This is a close-up image:
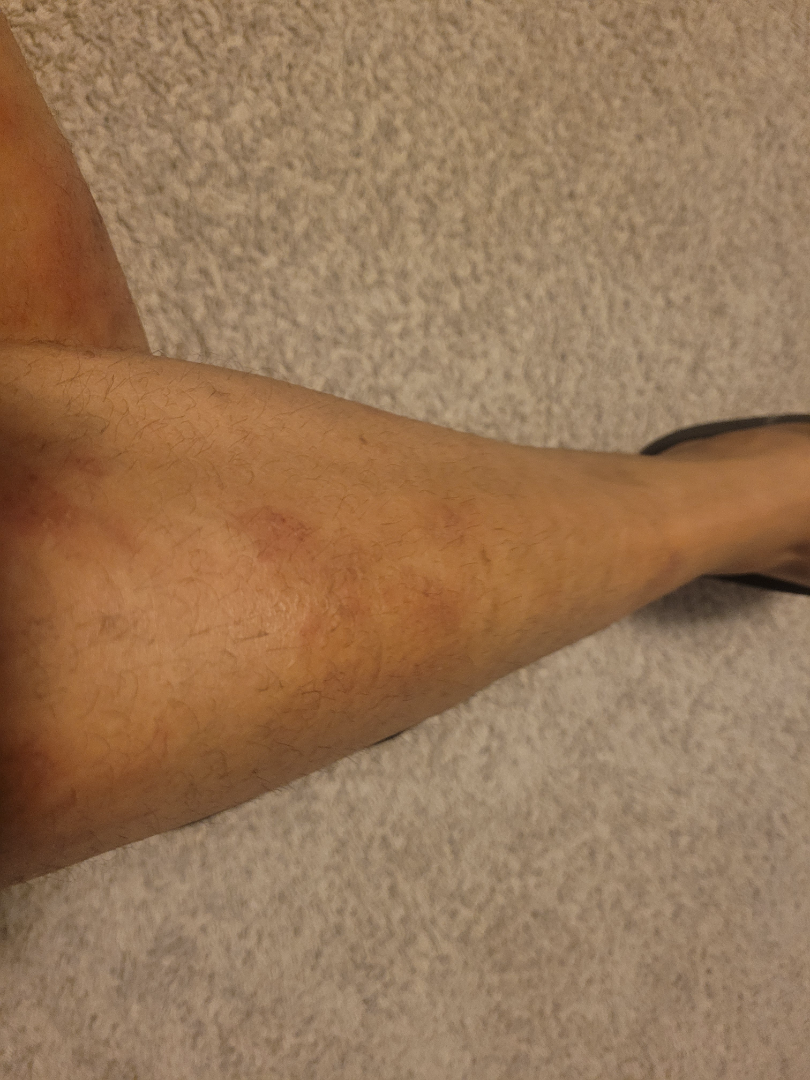Q: What was the assessment?
A: could not be assessed
Q: Reported symptoms?
A: itching
Q: What is the lesion texture?
A: raised or bumpy
Q: What is the patient's skin tone?
A: Fitzpatrick IV; lay reviewers estimated Monk skin tone scale 3
Q: When did this start?
A: one to four weeks